A dermatoscopic image of a skin lesion.
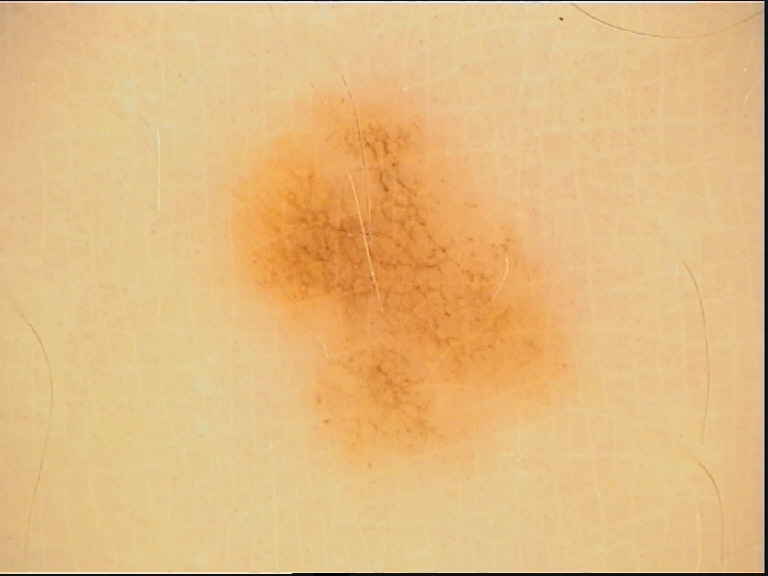Case:
- assessment: dysplastic junctional nevus (expert consensus)